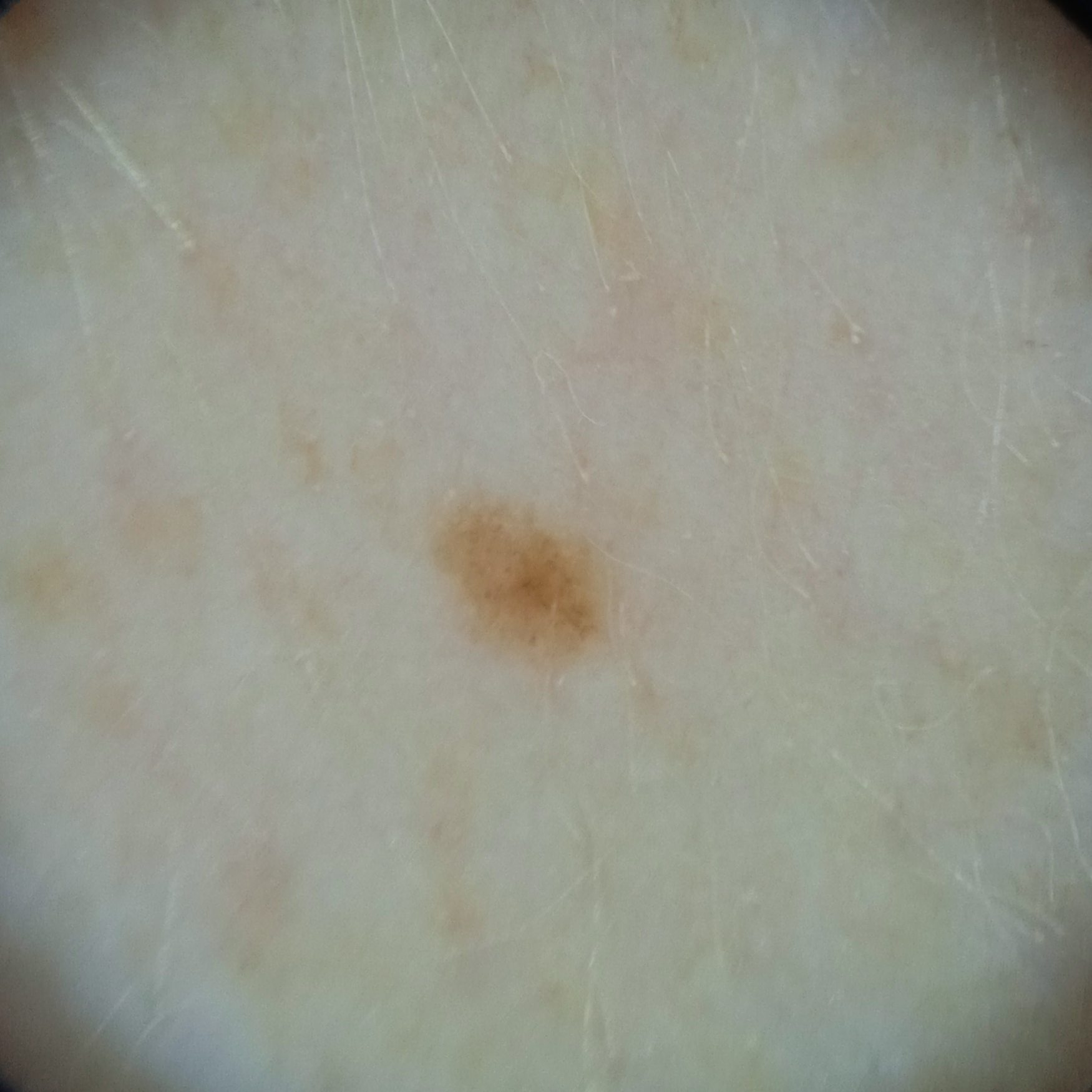A moderate number of moles by the patient's own estimate. Collected as part of a research study, without a referral diagnosis. Dermoscopy of a skin lesion. A female subject aged 50. The patient says their skin reddens painfully with sun exposure. The lesion is on an arm. Measuring roughly 2 mm. The diagnostic impression was a melanocytic nevus.